A dermoscopic image of a skin lesion.
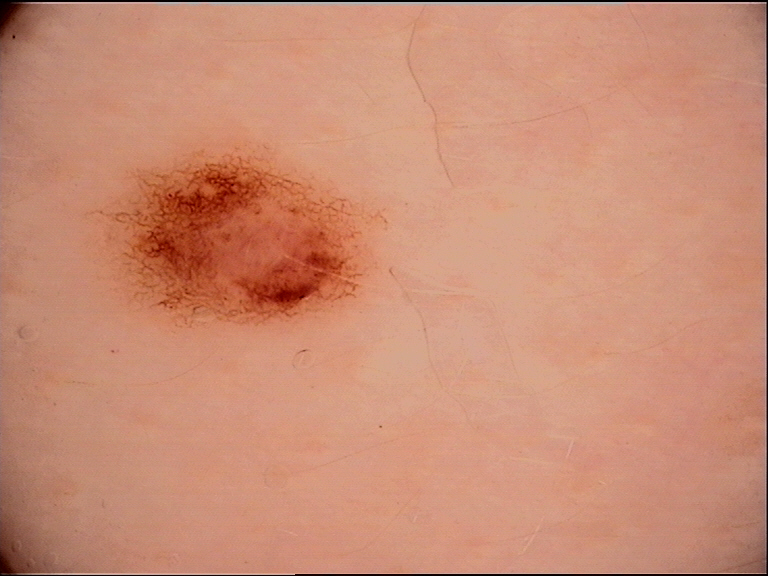Q: What is the diagnosis?
A: dysplastic junctional nevus (expert consensus)